A skin lesion imaged with a dermatoscope.
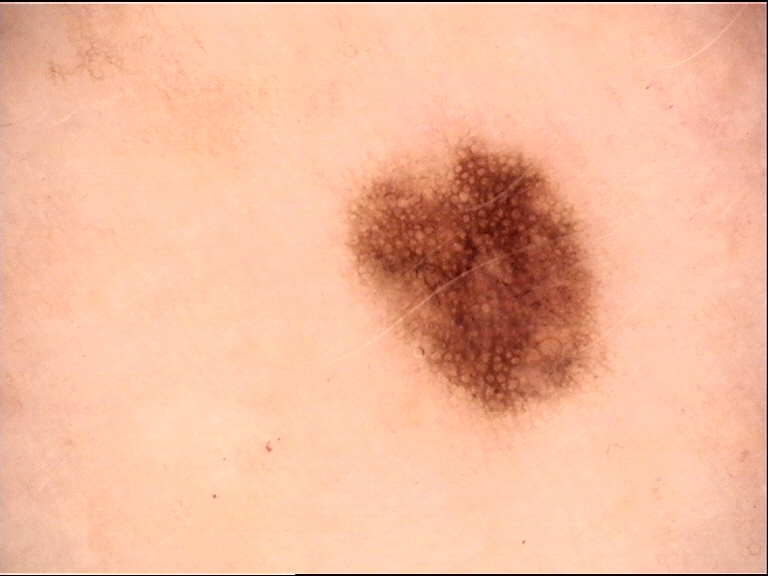The diagnosis was a benign lesion — a dysplastic junctional nevus.